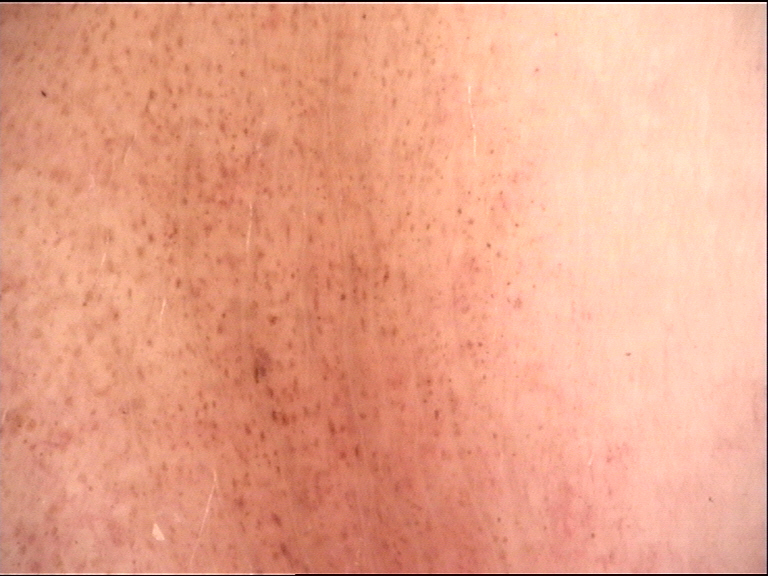modality: dermatoscopy
label: congenital junctional nevus (expert consensus)